Close-up view · the lesion involves the top or side of the foot:
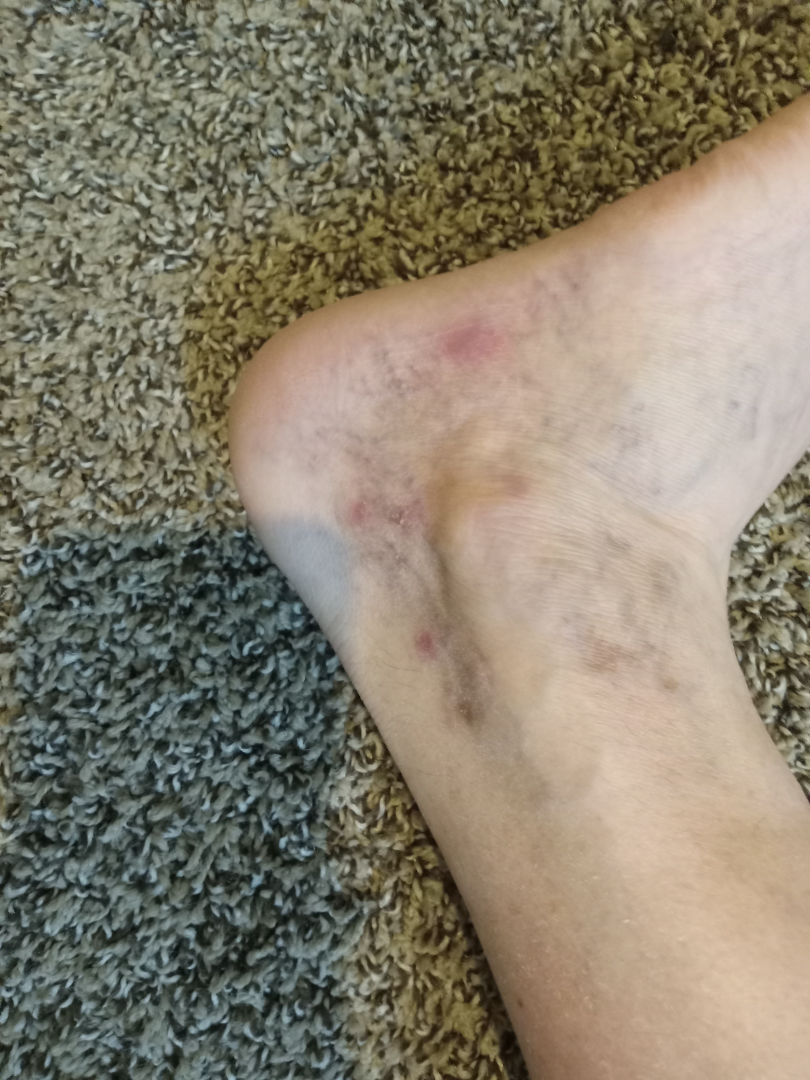Venous Stasis Ulcer (leading).